A dermoscopy image of a single skin lesion: 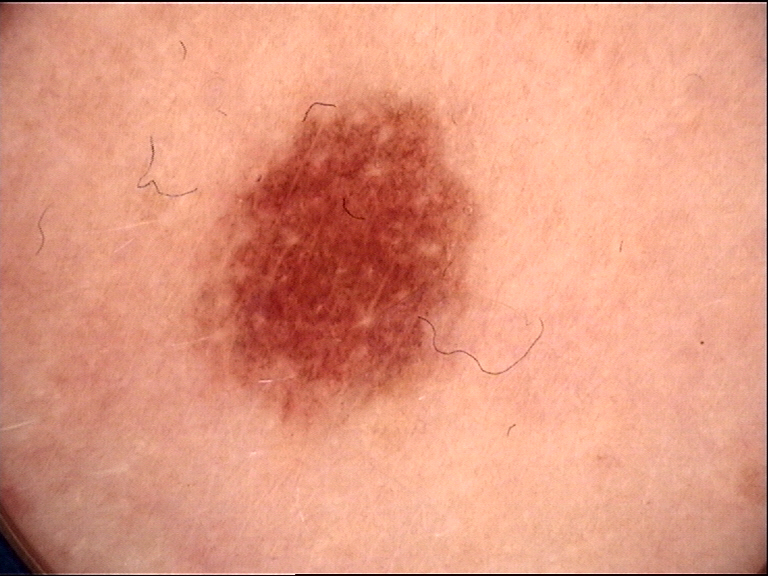Conclusion:
Consistent with a dysplastic junctional nevus.